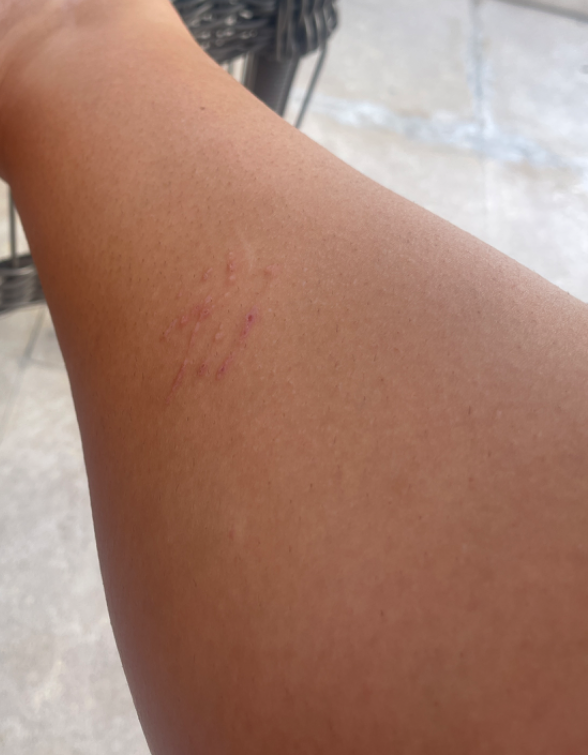Case summary:
– described texture — fluid-filled and raised or bumpy
– symptoms — enlargement, bothersome appearance, burning and itching
– self-categorized as — a rash
– body site — leg
– patient — female, age 18–29
– duration — one to four weeks
– other reported symptoms — none reported
– image framing — at a distance
– skin tone — Fitzpatrick phototype III; non-clinician graders estimated Monk Skin Tone 5 (US pool) or 3 (India pool)
– impression — most likely Animal bite - wound; also raised was Abrasion, scrape, or scab; also consider Inflicted skin lesions